Dermoscopy of a skin lesion. Referred for assessment of suspected melanocytic nevus: 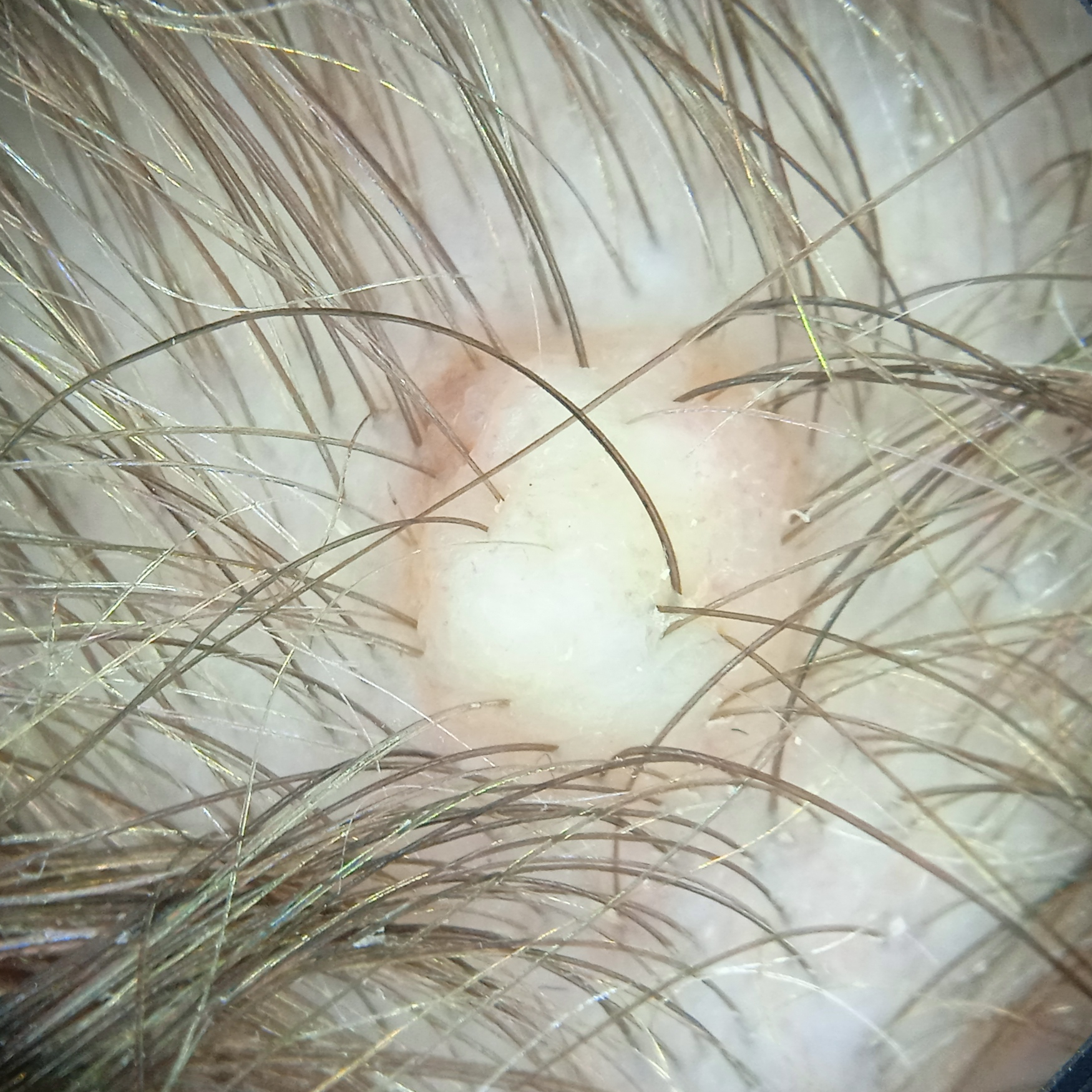<skin_lesion>
<diagnosis>
<name>melanocytic nevus</name>
<malignancy>benign</malignancy>
<procedure>excision</procedure>
</diagnosis>
</skin_lesion>